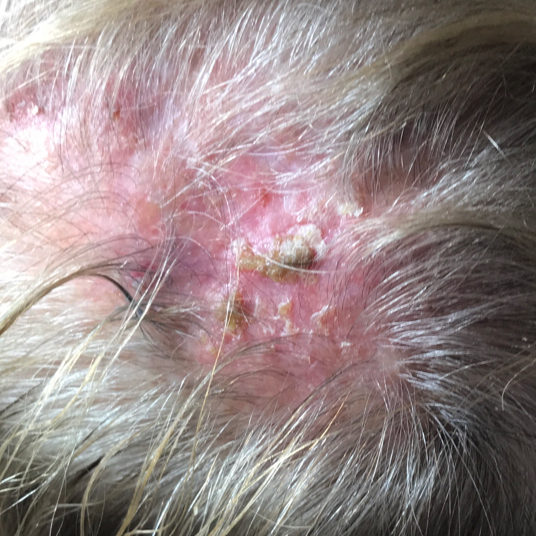A female subject age 83. A clinical photo of a skin lesion taken with a smartphone. Per patient report, the lesion hurts and itches. Histopathologically confirmed as an actinic keratosis.